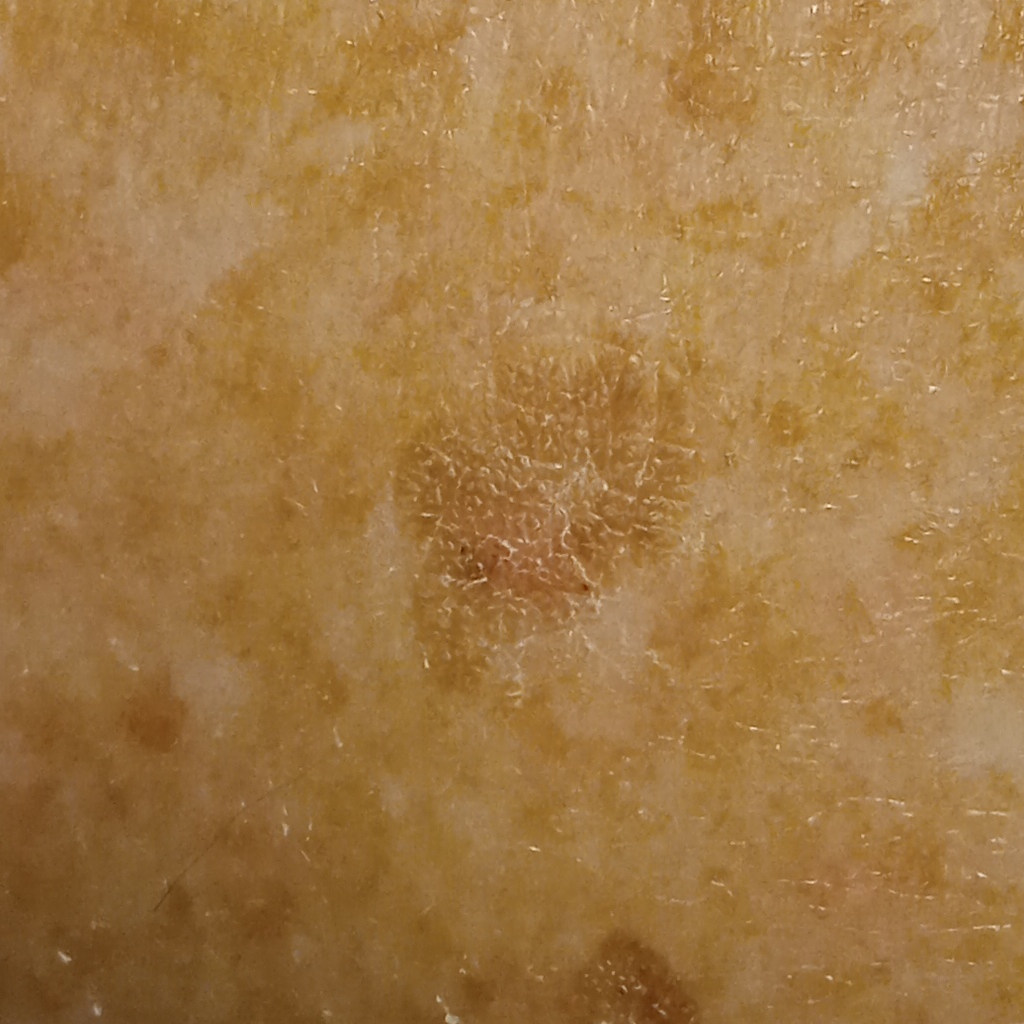Q: What was the diagnosis?
A: seborrheic keratosis (dermatologist consensus)